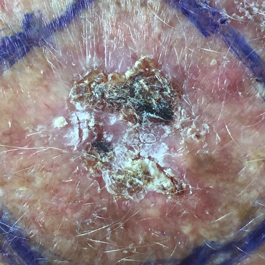A female subject in their 80s. A clinical photo of a skin lesion taken with a smartphone. History notes prior malignancy (patient or family). Recorded as skin type II. Located on the face. The lesion measures 15 × 13 mm. Per patient report, the lesion has grown, hurts, is elevated, itches, and has bled, but has not changed. Histopathological examination showed a basal cell carcinoma.